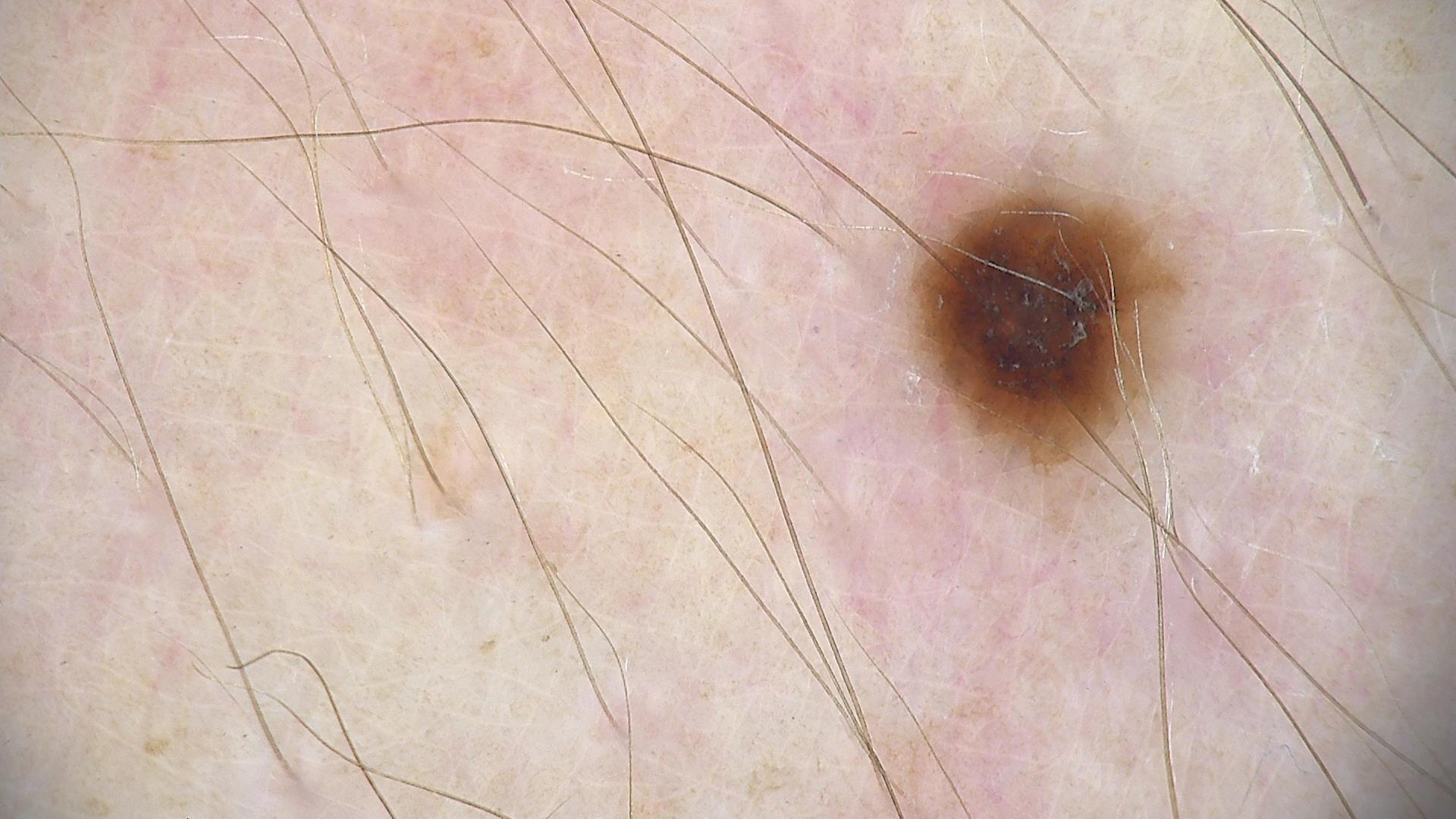{
  "diagnosis": {
    "name": "dysplastic junctional nevus",
    "code": "jd",
    "malignancy": "benign",
    "super_class": "melanocytic",
    "confirmation": "expert consensus"
  }
}